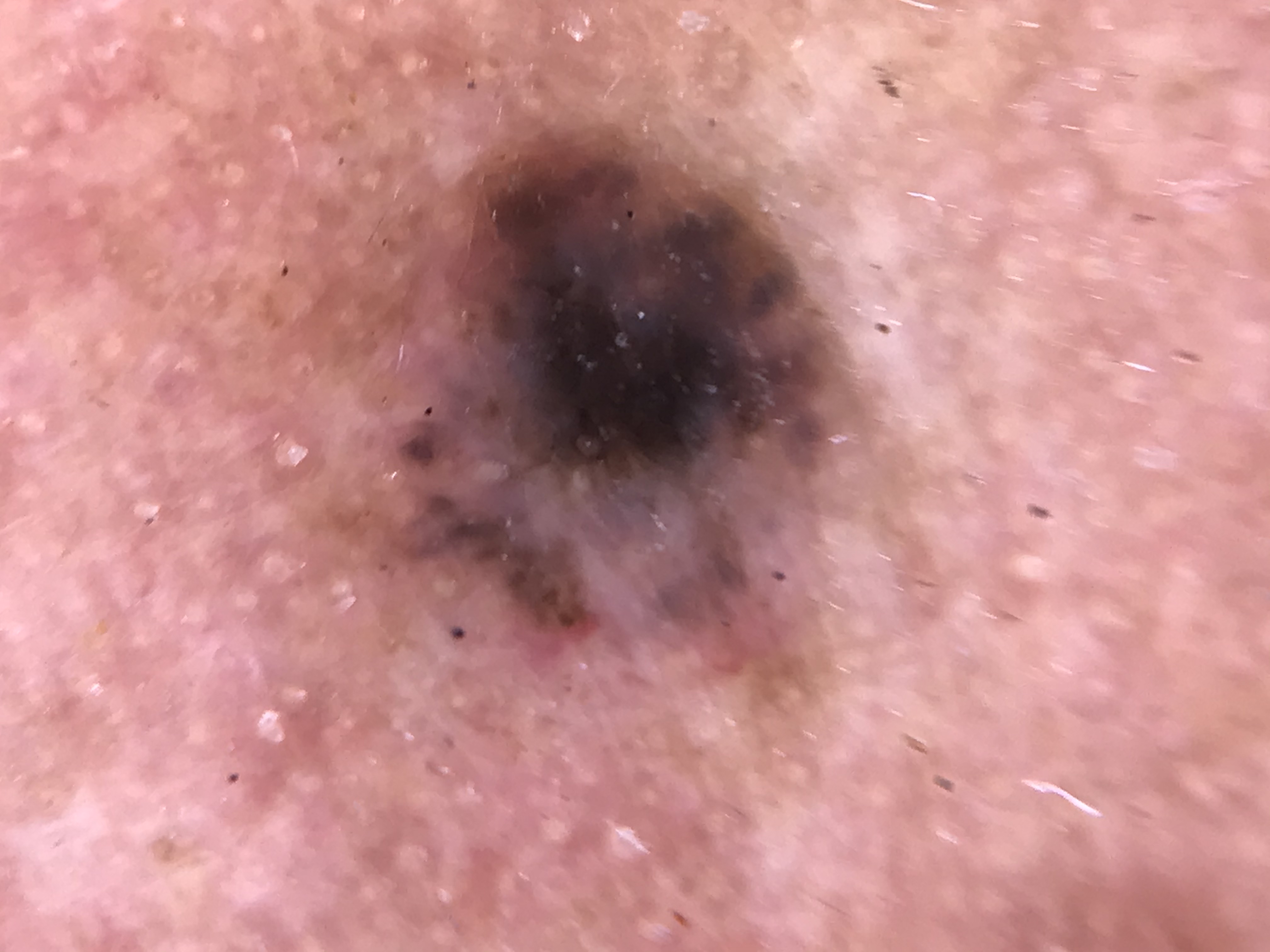A dermatoscopic image of a skin lesion.
The morphology is that of a keratinocytic lesion.
Histopathology confirmed a malignancy — a basal cell carcinoma.